A female subject, in their mid- to late 50s · a dermoscopy image of a single skin lesion — 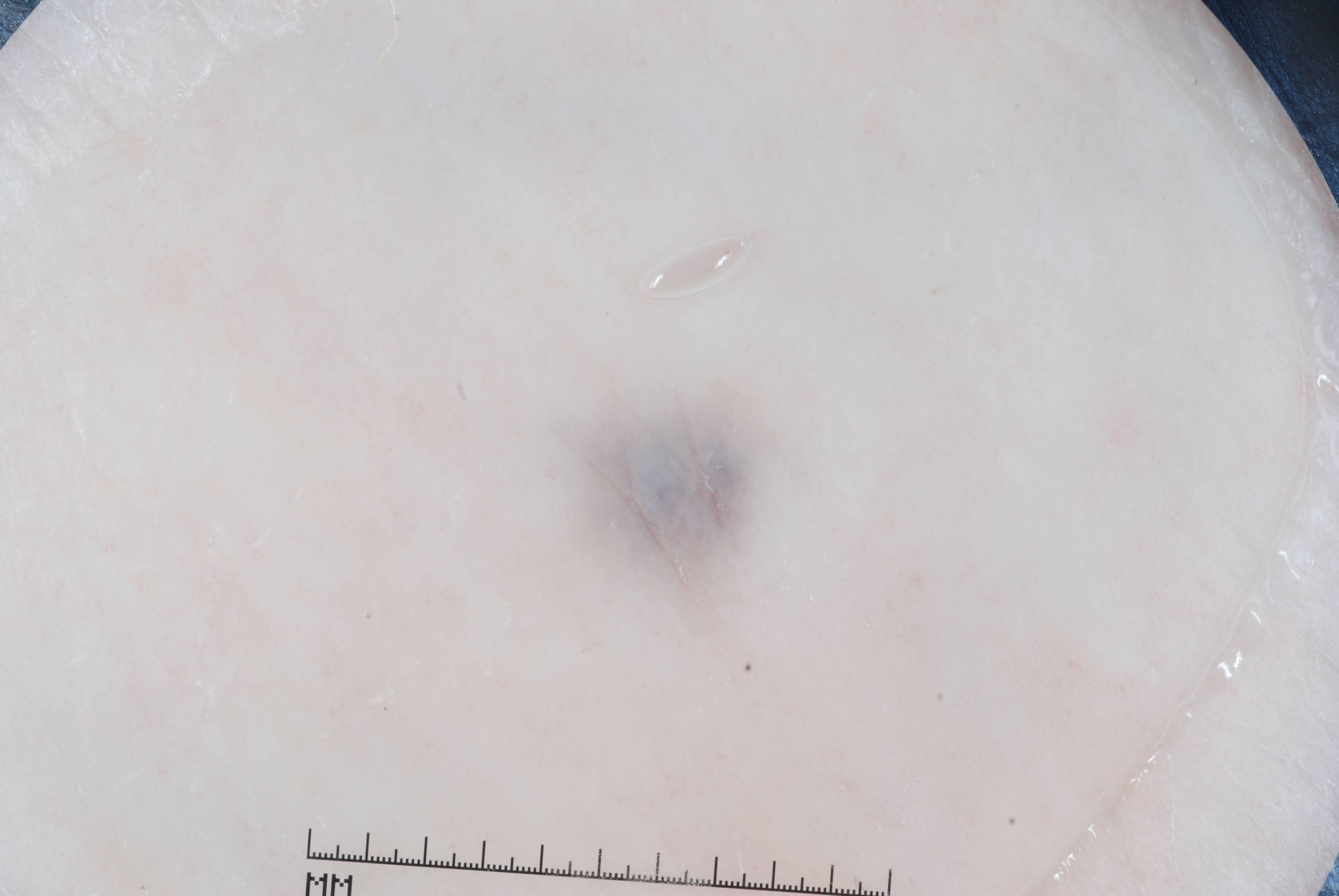<lesion>
  <lesion_location>
    <bbox_xyxy>575, 406, 753, 595</bbox_xyxy>
  </lesion_location>
  <dermoscopic_features>
    <present/>
    <absent>pigment network, milia-like cysts, negative network, streaks</absent>
  </dermoscopic_features>
  <diagnosis>
    <name>melanocytic nevus</name>
    <malignancy>benign</malignancy>
    <lineage>melanocytic</lineage>
    <provenance>clinical</provenance>
  </diagnosis>
</lesion>